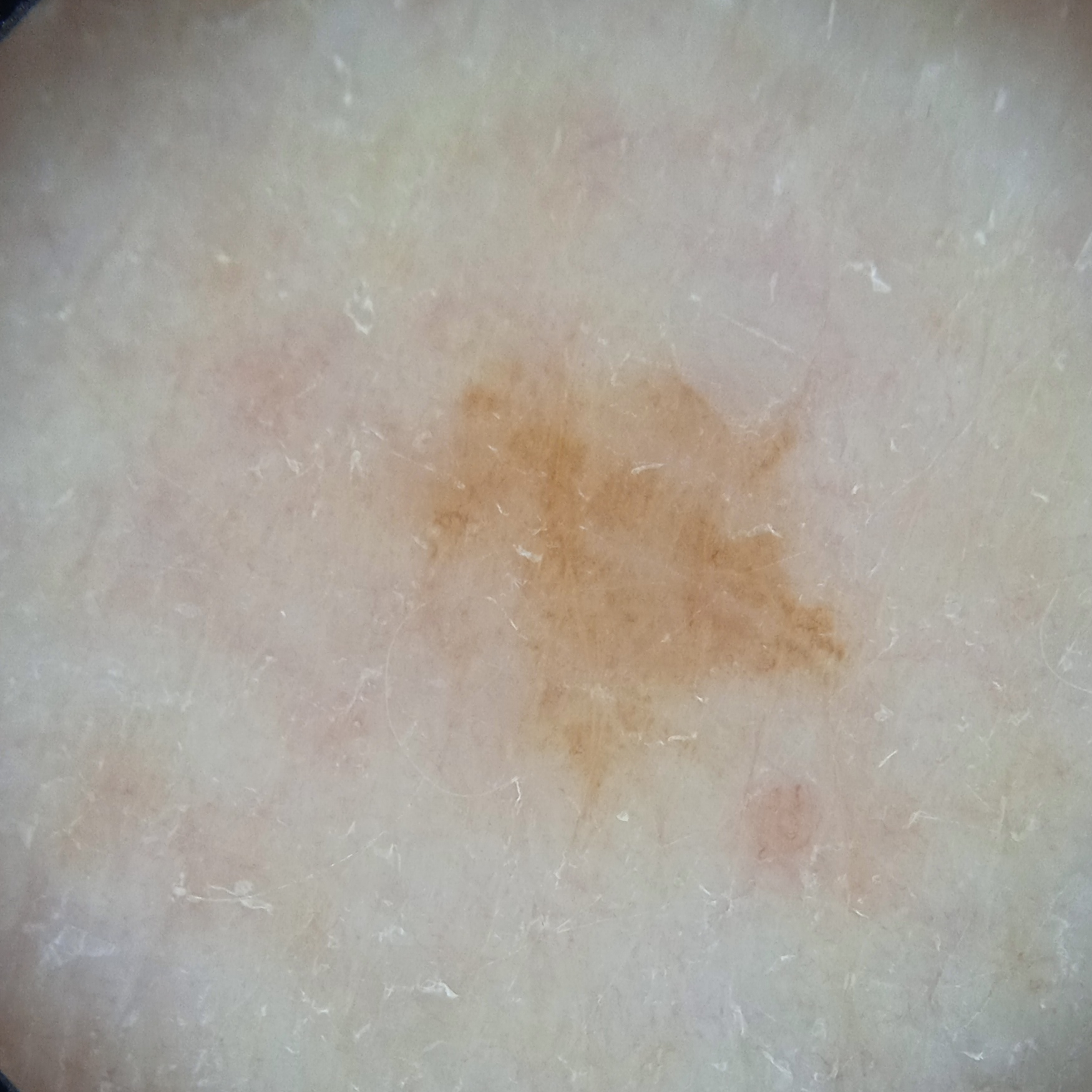<record>
  <mole_burden>few melanocytic nevi overall</mole_burden>
  <sun_reaction>skin reddens with sun exposure</sun_reaction>
  <patient>
    <age>71</age>
    <sex>female</sex>
  </patient>
  <referral>research study (no referral diagnosis)</referral>
  <risk_factors>
    <positive>a personal history of cancer, a personal history of skin cancer</positive>
  </risk_factors>
  <image>dermoscopic image</image>
  <lesion_location>an arm</lesion_location>
  <lesion_size>
    <diameter_mm>6.1</diameter_mm>
  </lesion_size>
  <diagnosis>
    <name>melanocytic nevus</name>
    <malignancy>benign</malignancy>
  </diagnosis>
</record>